A skin lesion imaged with contact-polarized dermoscopy — 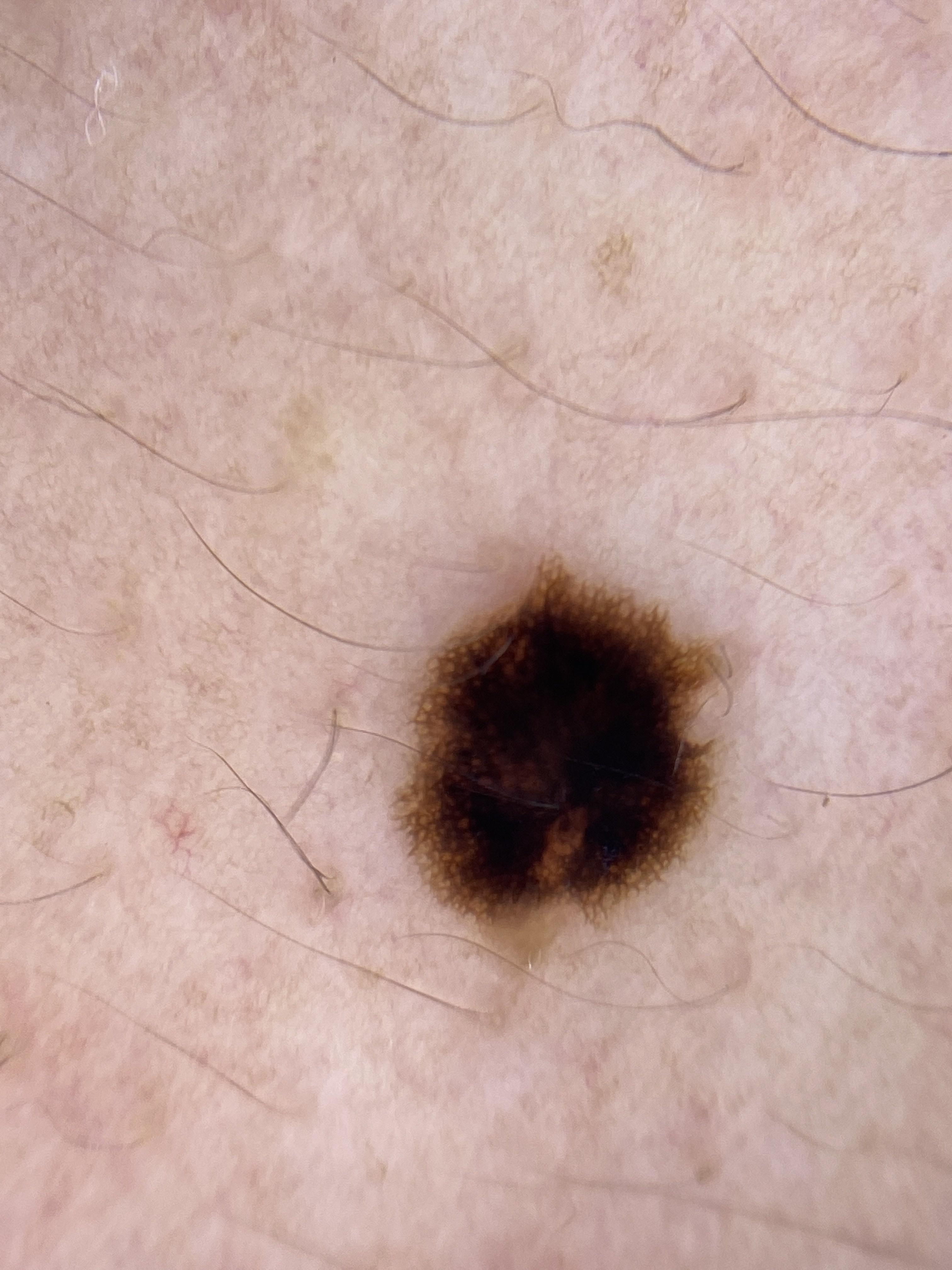Clinical context: The lesion involves the trunk (the posterior trunk). Diagnosis: Confirmed on histopathology as a melanocytic lesion — a nevus.